Close-up view · located on the top or side of the foot — 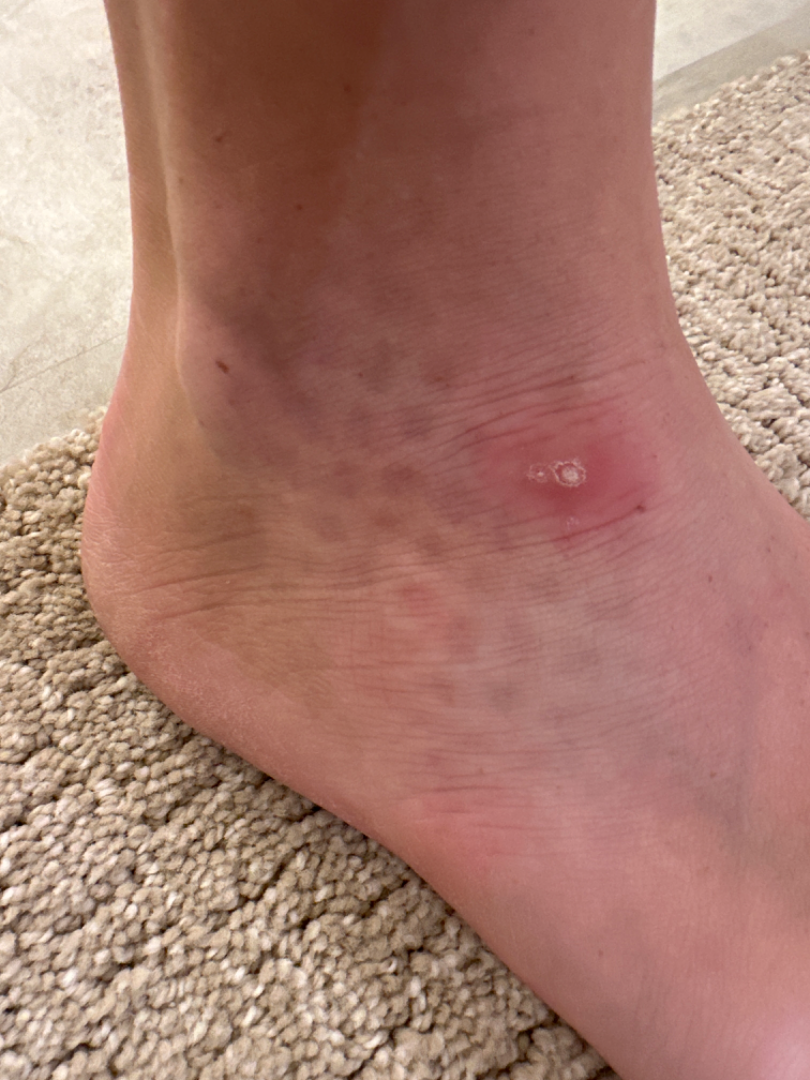On teledermatology review, the differential is split between Clavus and Insect Bite.